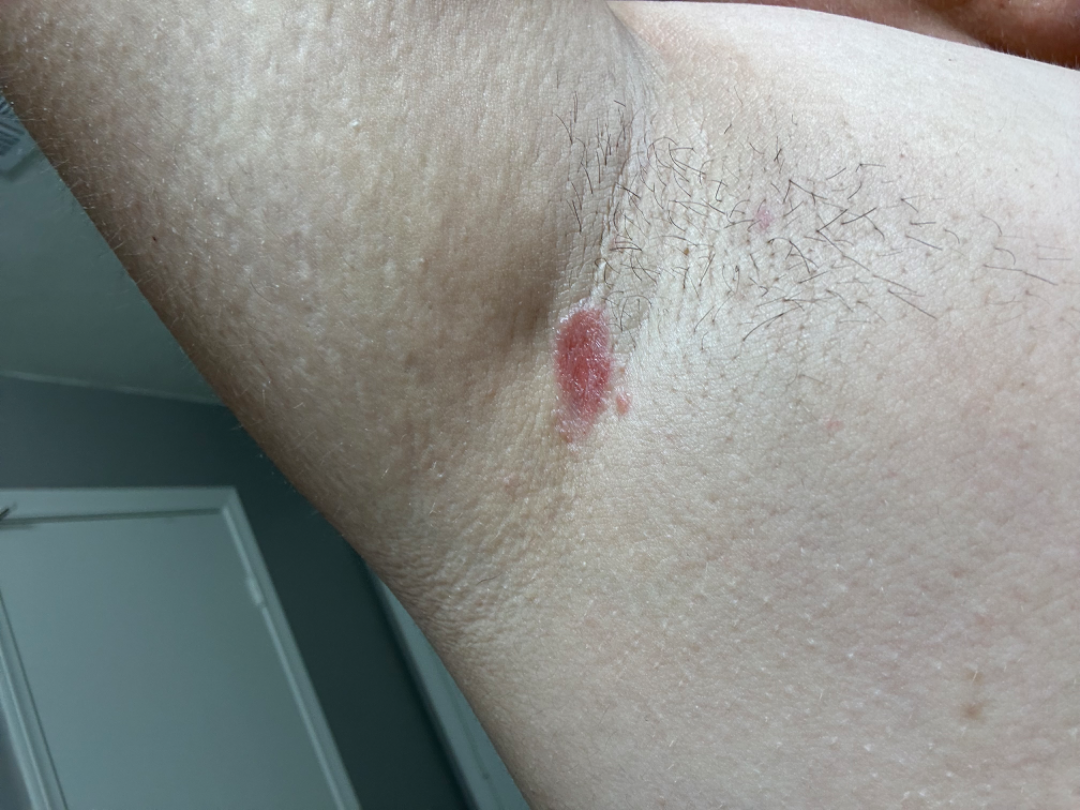  shot_type: close-up
  differential:
    tied_lead:
      - Intertrigo
      - granular parakeratosis